This image was taken at a distance · the patient reports the lesion is rough or flaky and raised or bumpy · the patient also reports joint pain · the patient reports the condition has been present for more than one year · the patient reports bothersome appearance, pain and enlargement · the affected area is the back of the hand · the subject is 30–39, female — 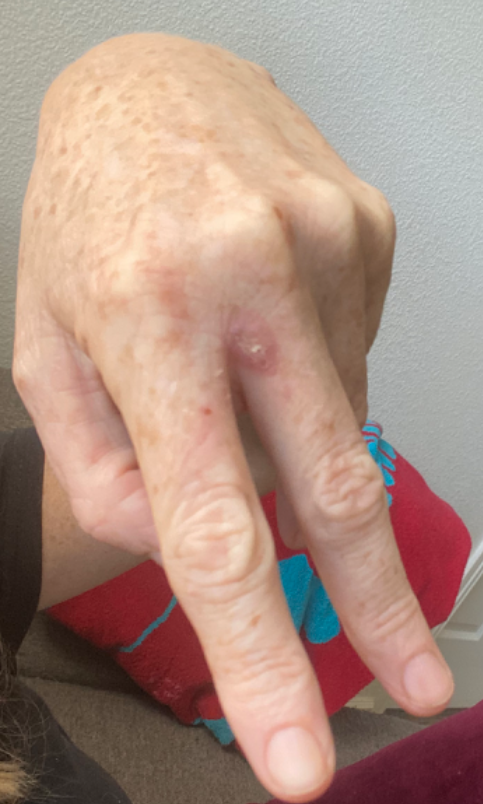The reviewing dermatologist was unable to assign a differential diagnosis from the image.